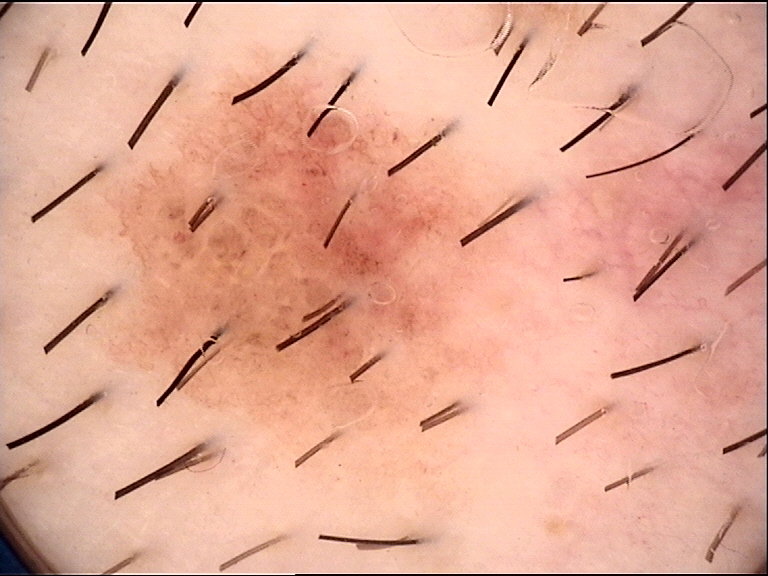modality: dermatoscopy, diagnosis: dysplastic compound nevus (expert consensus).